The subject is a male aged 68-72 · a dermoscopic image of a skin lesion: 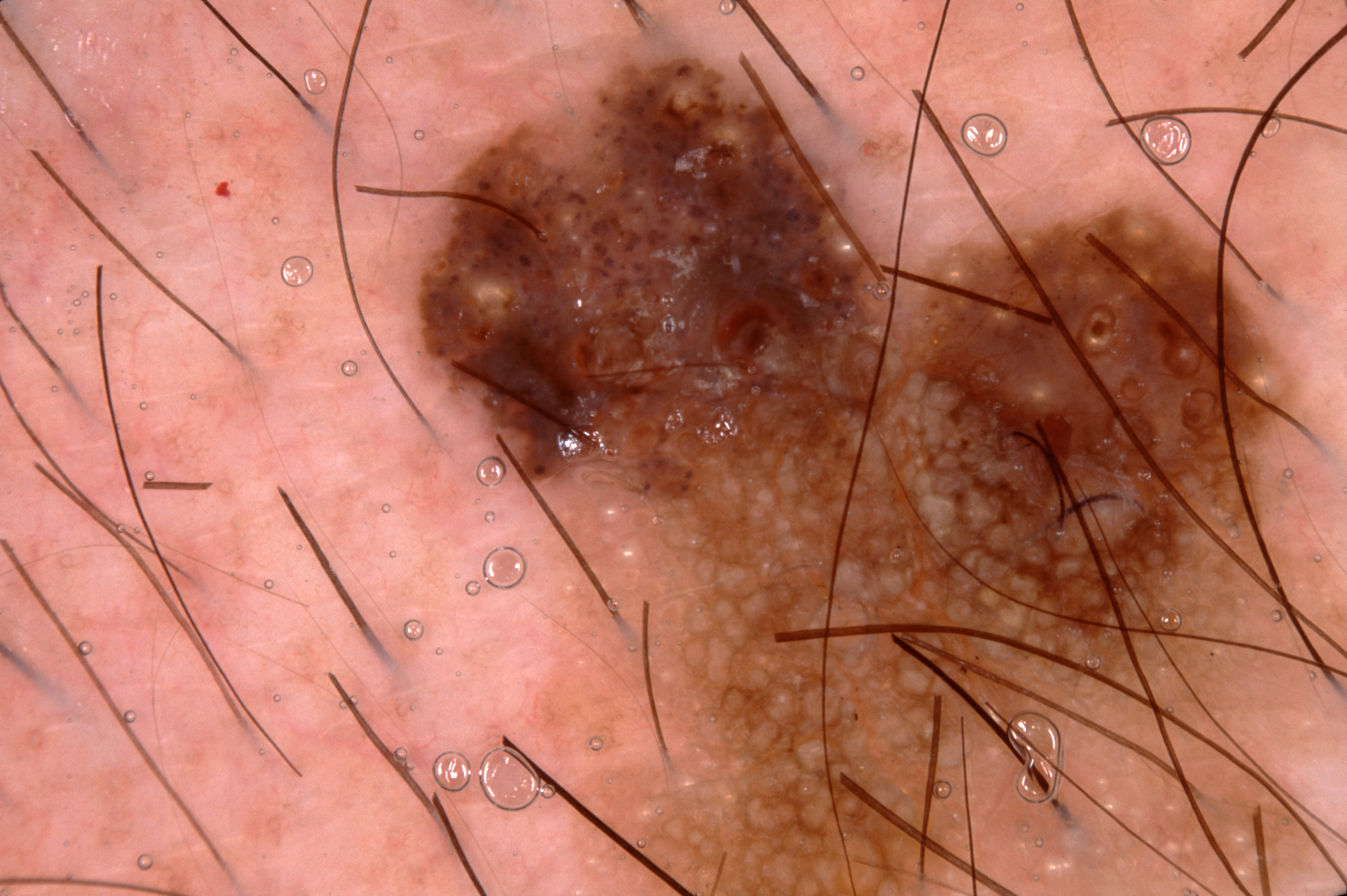Image and clinical context:
A prominent lesion filling much of the field. Dermoscopic assessment notes milia-like cysts; no streaks, pigment network, or negative network. As (left, top, right, bottom), the lesion's extent is [410,56,1294,889].
Impression:
Clinically diagnosed as a seborrheic keratosis, a benign skin lesion.